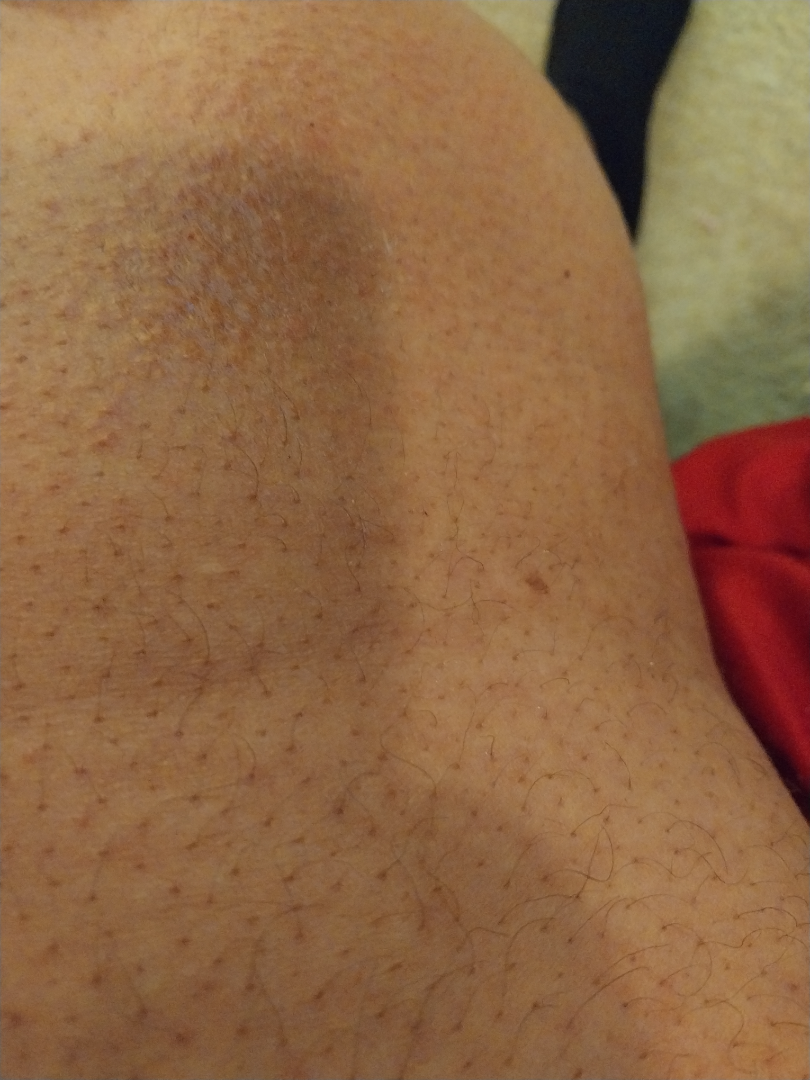The dermatologist could not determine a likely condition from the photograph alone. A close-up photograph. The subject is 50–59, female. Located on the leg.